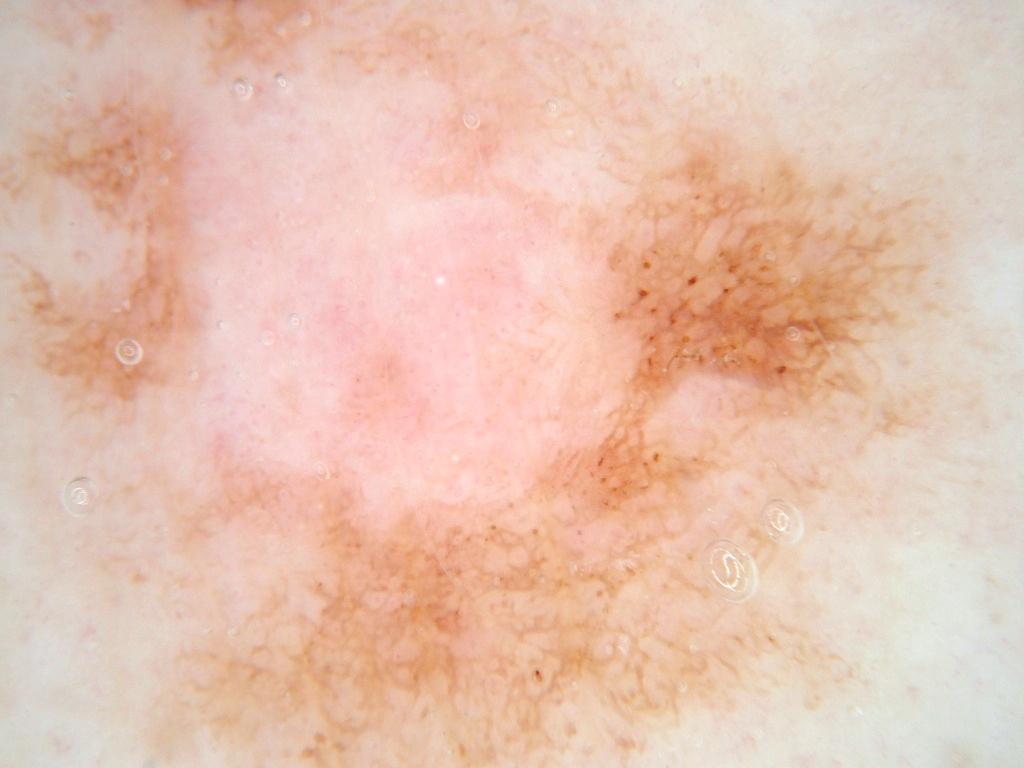{
  "image": {
    "modality": "dermoscopy"
  },
  "patient": {
    "sex": "female",
    "age_approx": 50
  },
  "dermoscopic_features": {
    "present": [
      "pigment network"
    ],
    "absent": [
      "streaks",
      "negative network",
      "globules",
      "milia-like cysts"
    ]
  },
  "lesion_location": "spans the dermoscopic field",
  "diagnosis": {
    "name": "melanocytic nevus",
    "malignancy": "benign",
    "lineage": "melanocytic",
    "provenance": "clinical"
  }
}